Recorded as skin type II · a female patient approximately 50 years of age: 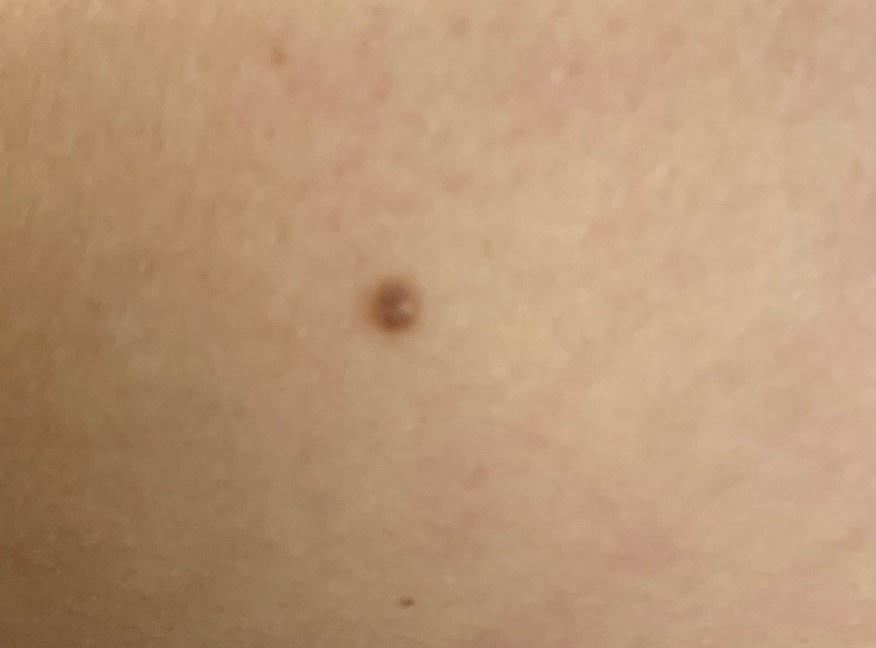| key | value |
|---|---|
| anatomic site | a lower extremity |
| impression | Dermatofibroma |